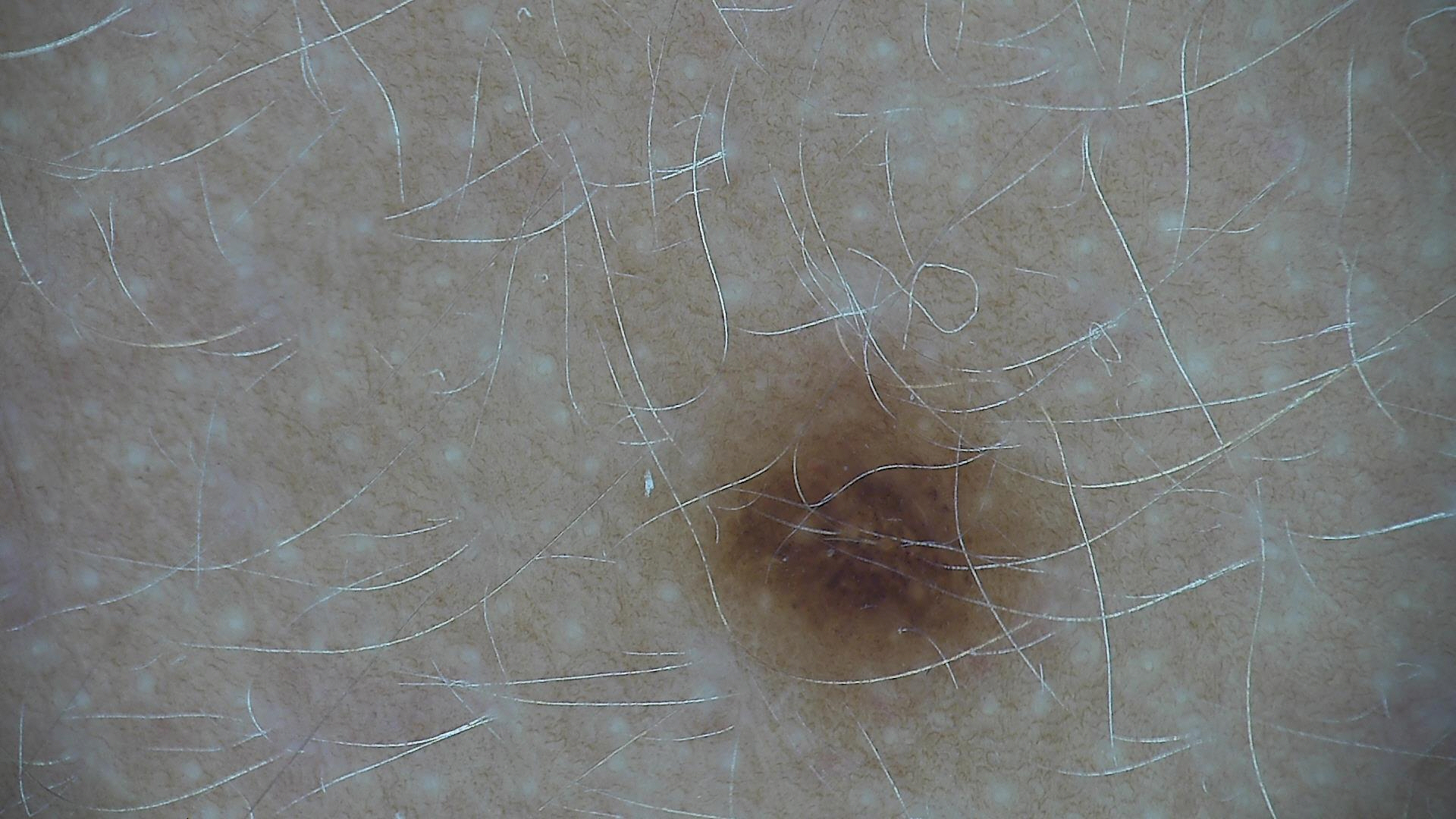Classified as a dysplastic junctional nevus.